Acquired for a research image collection, with no referral diagnosis; the patient says their skin reddens with sun exposure; by self-report, a history of sunbed use and no immunosuppression; a dermoscopic image of a skin lesion:
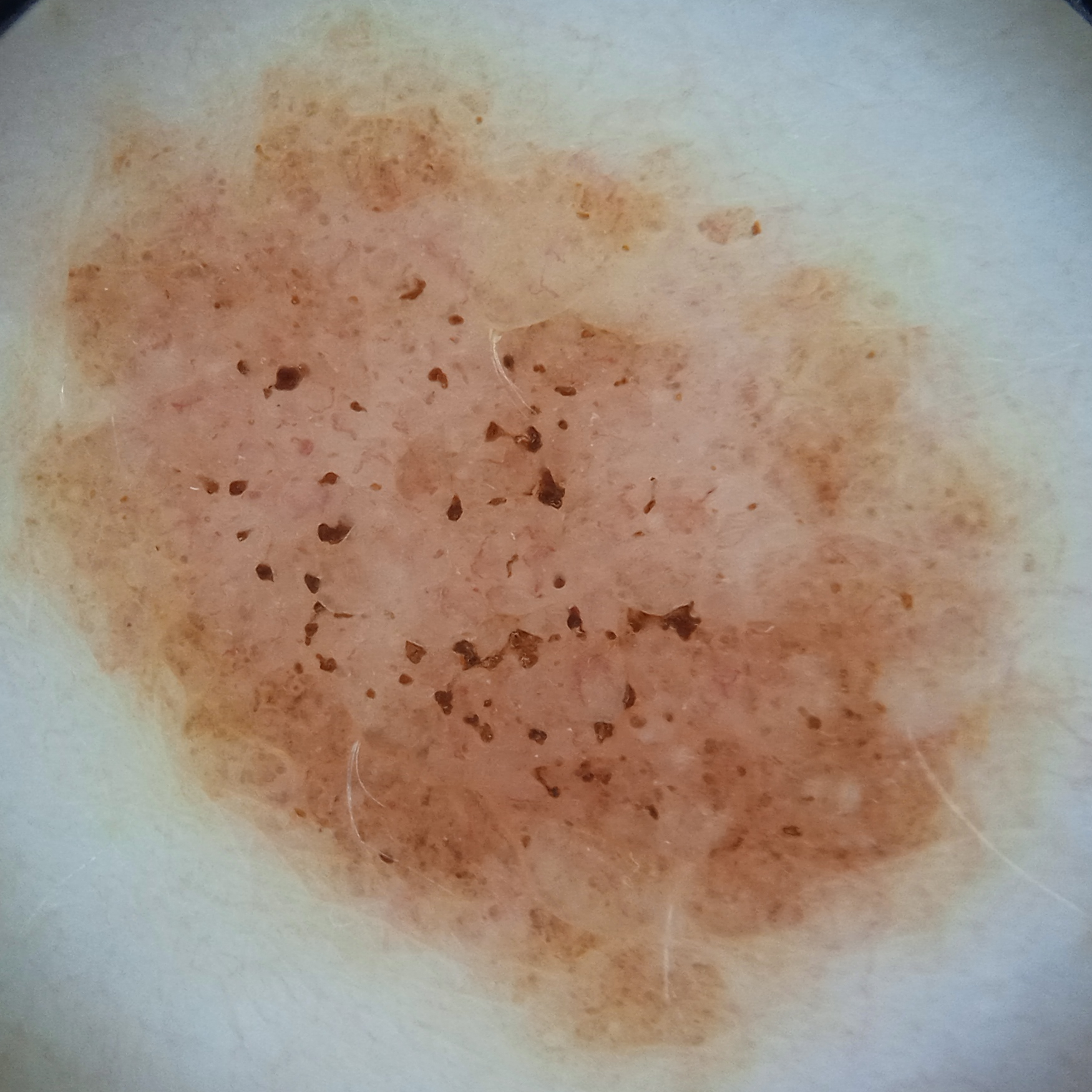Located on the torso. The lesion measures approximately 13 mm. Four dermatologists reviewed the lesion; the consensus was a melanocytic nevus; there was some disagreement among the reviewers; diagnostic confidence was good.